A dermoscopic image of a skin lesion:
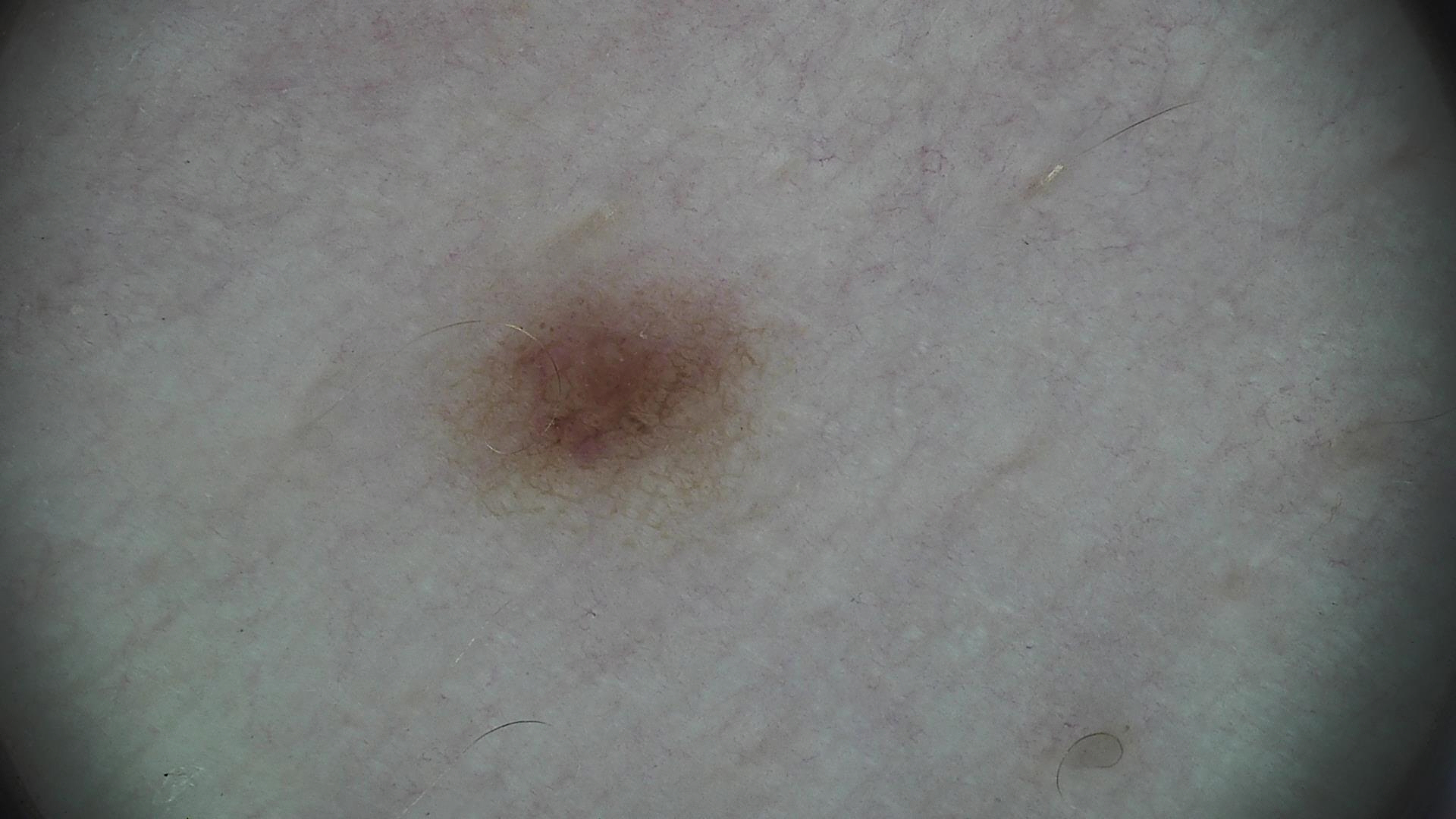The diagnostic label was a dysplastic junctional nevus.